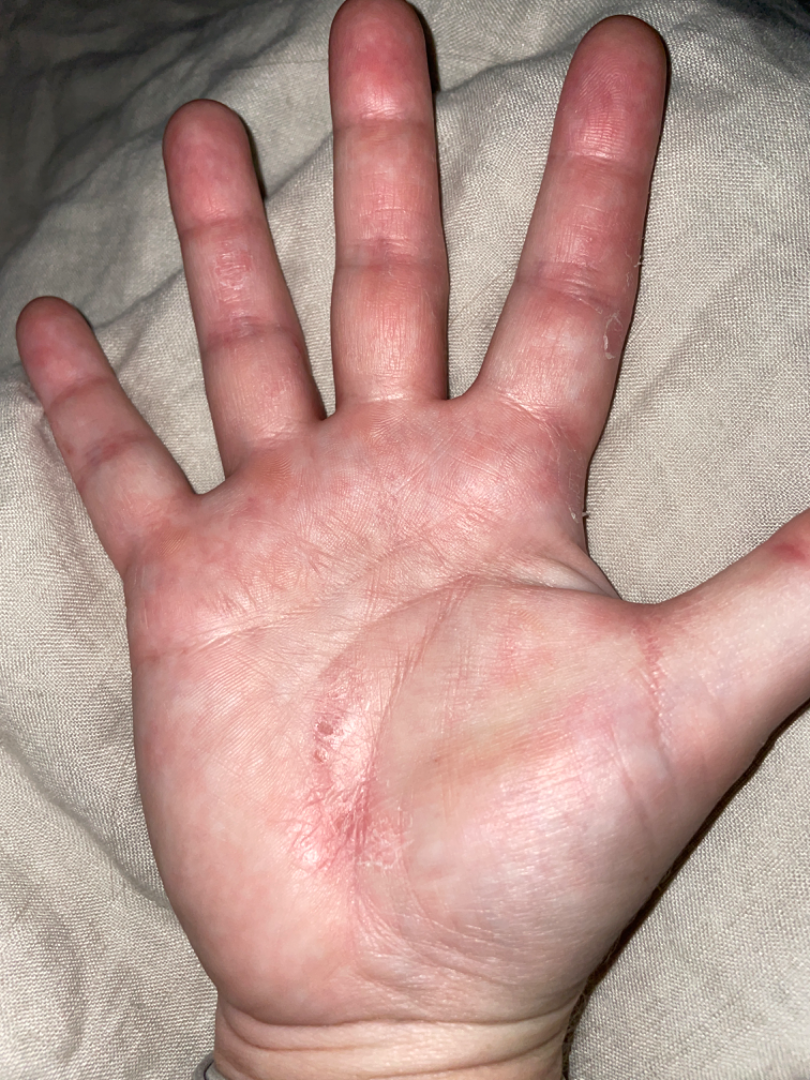affected area=palm; image framing=at a distance; dermatologist impression=the differential, in no particular order, includes Psoriasis, Eczema and Allergic Contact Dermatitis.